A dermoscopic close-up of a skin lesion: 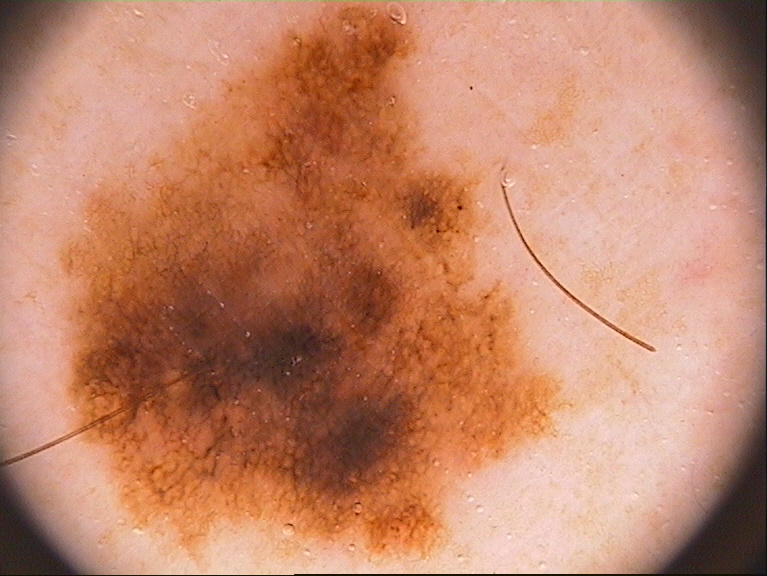Findings:
As (left, top, right, bottom), the lesion is located at <bbox>56, 4, 570, 570</bbox>. Dermoscopic assessment notes globules and pigment network. The lesion takes up about 47% of the image.
Conclusion:
Biopsy-confirmed as a melanoma.